Dermoscopy of a skin lesion.
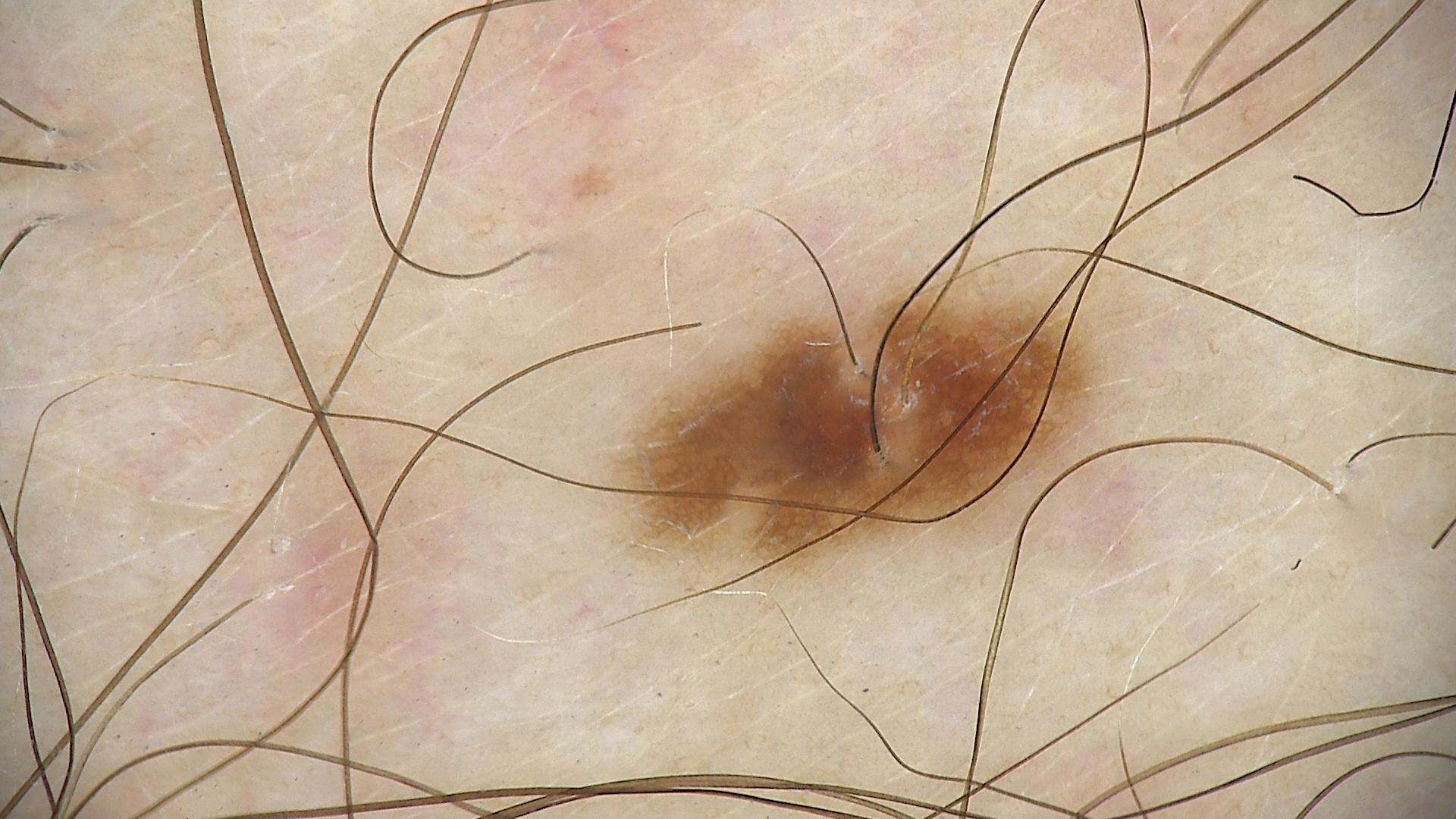class = dysplastic junctional nevus (expert consensus).